The photograph is a close-up of the affected area.
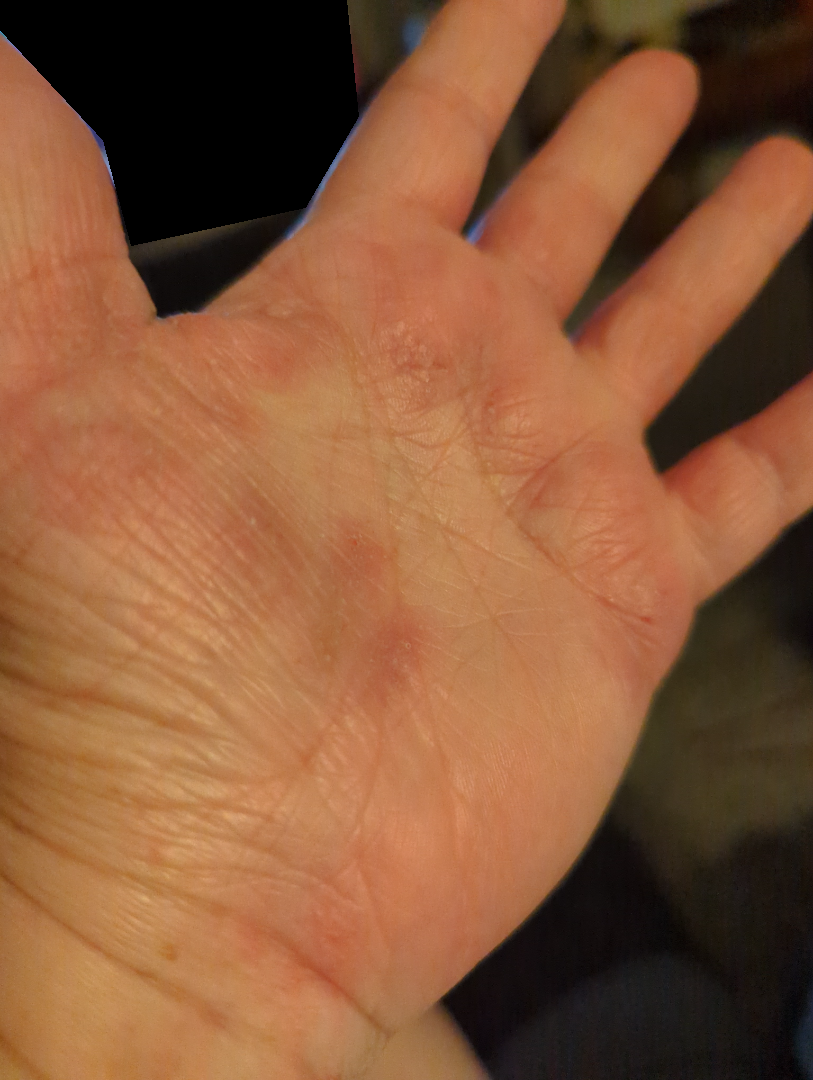{"differential": {"leading": ["Eczema"]}}